The back of the torso and front of the torso are involved. Present for one to three months. No relevant systemic symptoms. No associated lesion symptoms were reported. The patient is a male aged 30–39. The patient considered this a rash. The lesion is described as flat. The photograph was taken at an angle.
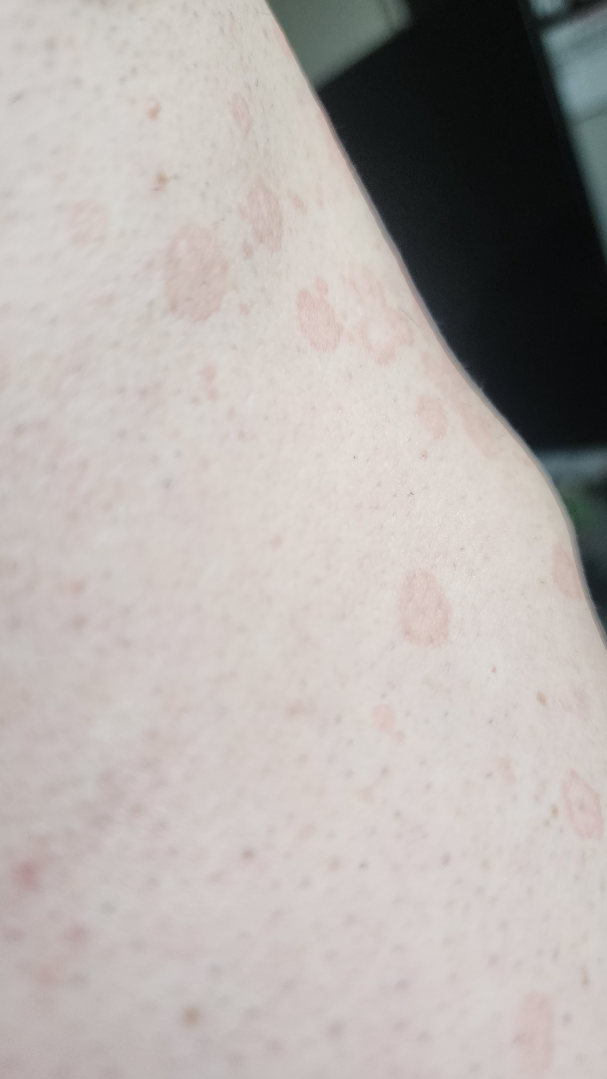On photographic review, most likely Psoriasis; a remote consideration is Pityriasis rosea; lower on the differential is Tinea Versicolor; less probable is Parapsoriasis; less likely is Seborrheic Dermatitis.